The subject is a male aged 50–59. The patient indicates the condition has been present for three to twelve months. Symptoms reported: bothersome appearance and enlargement. The photo was captured at an angle. The patient indicates the lesion is raised or bumpy: 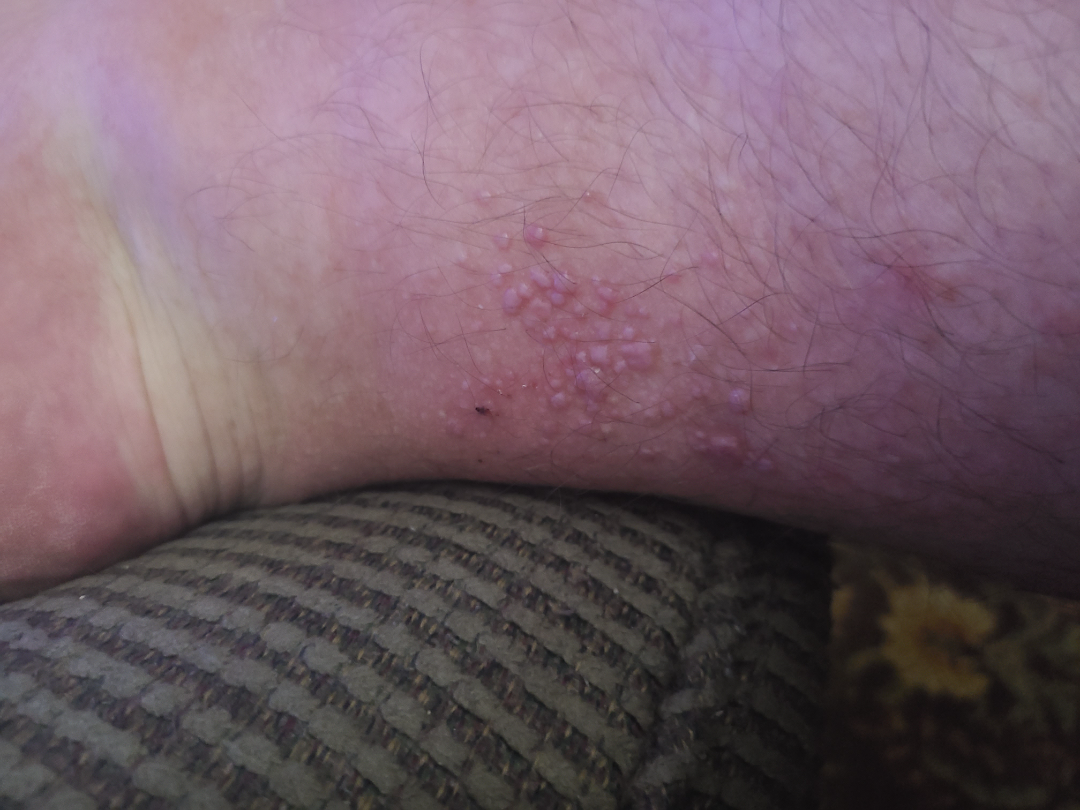Impression: On photographic review: Molluscum Contagiosum (favored); Verruca vulgaris (considered); Calcinosis cutis (remote).